This is a close-up image; the leg is involved; male subject, age 30–39.
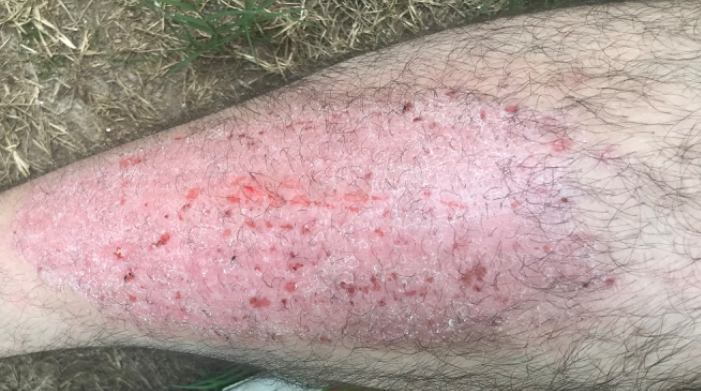differential = one reviewing dermatologist: the impression is Lichen Simplex Chronicus